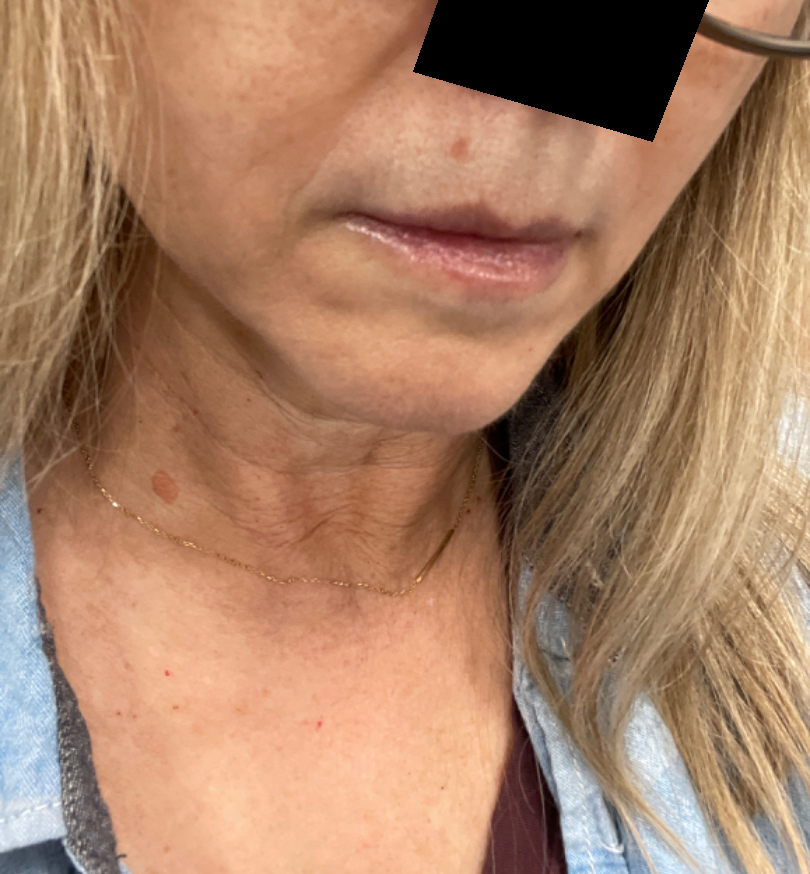patient: female, age 50–59; location: head or neck; image framing: at an angle; impression: the differential, in no particular order, includes Actinic Keratosis, Basal Cell Carcinoma and SCC/SCCIS.